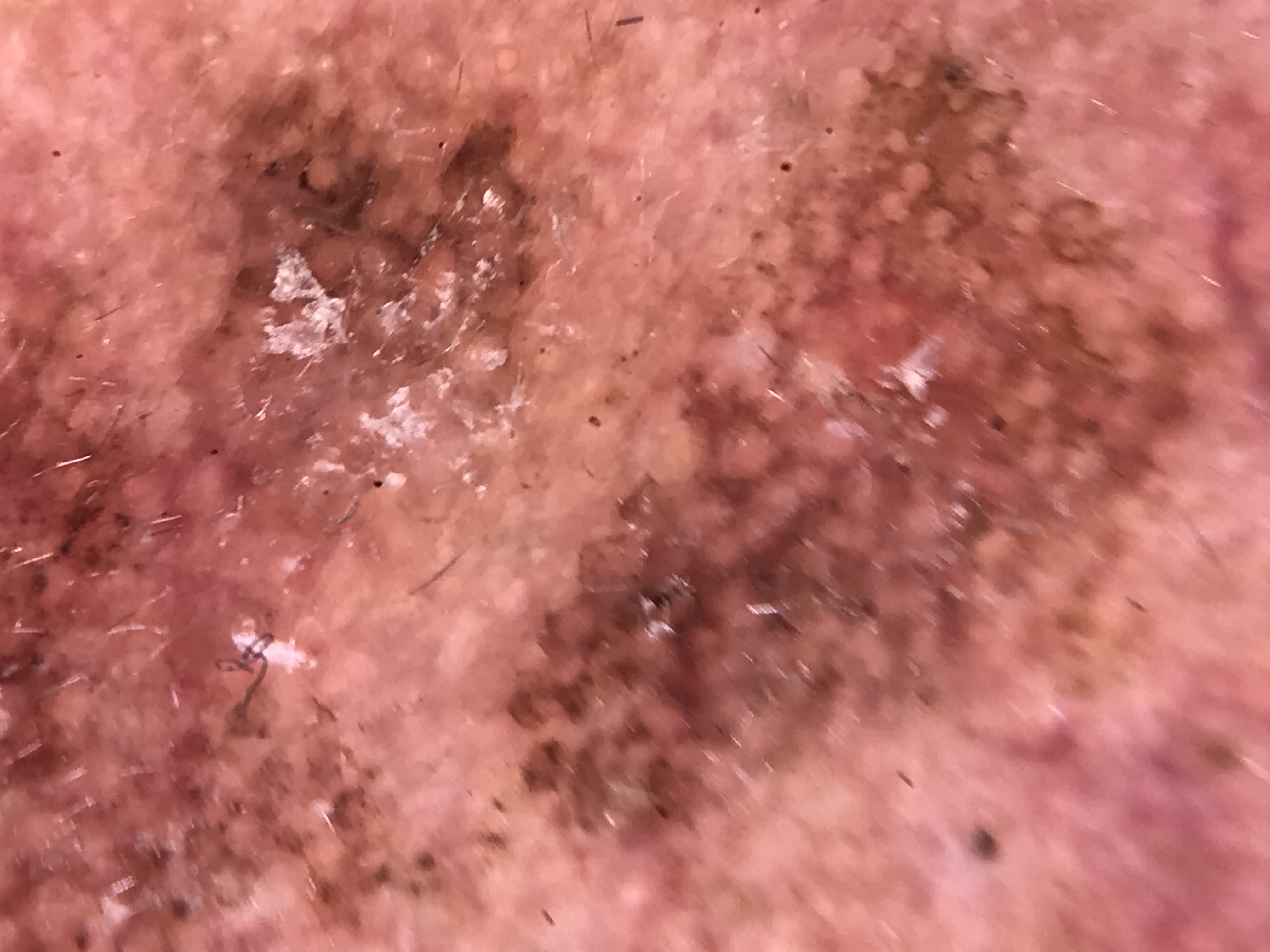image = dermoscopy; class = actinic keratosis (expert consensus).